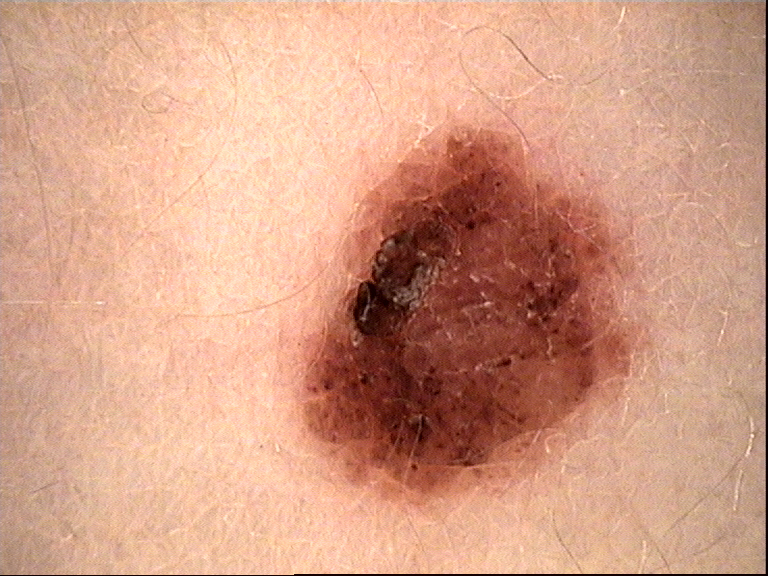| feature | finding |
|---|---|
| label | compound nevus (expert consensus) |